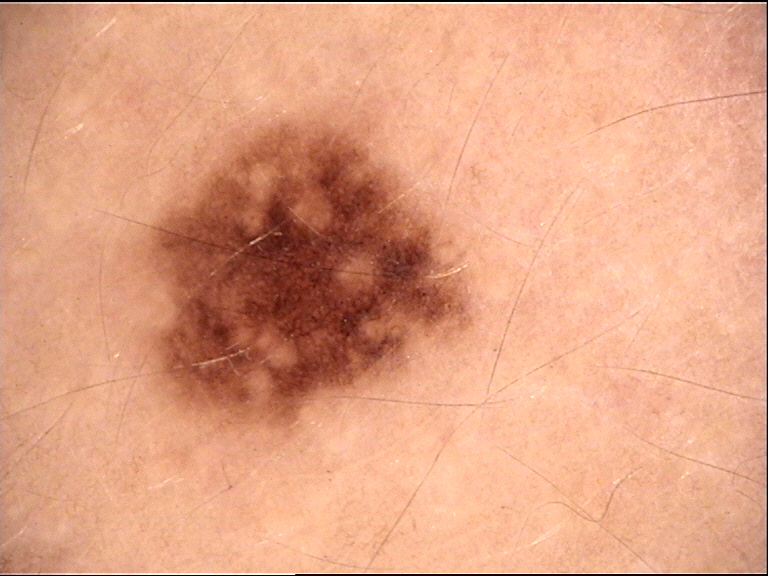A dermoscopic close-up of a skin lesion.
The diagnostic label was a benign lesion — a dysplastic junctional nevus.